Located on the back of the torso, the photograph is a close-up of the affected area: 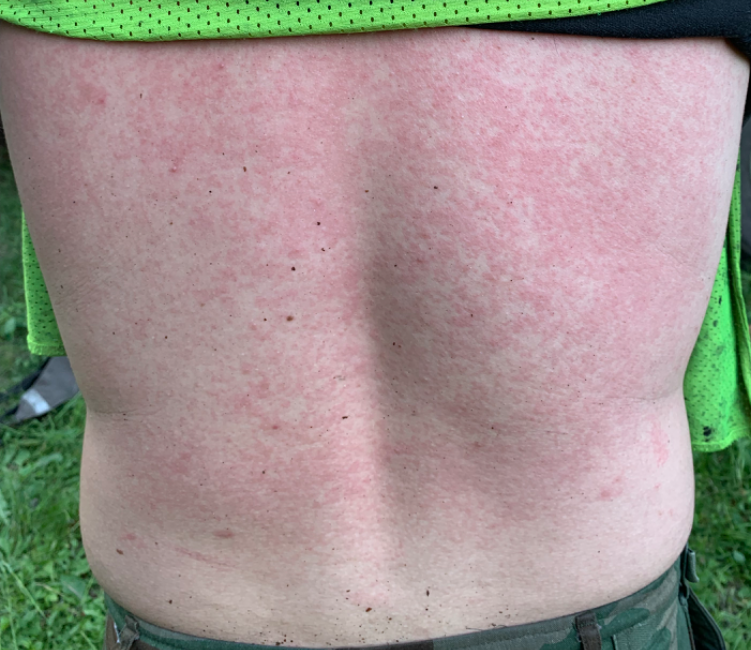Q: What was the assessment?
A: not assessable